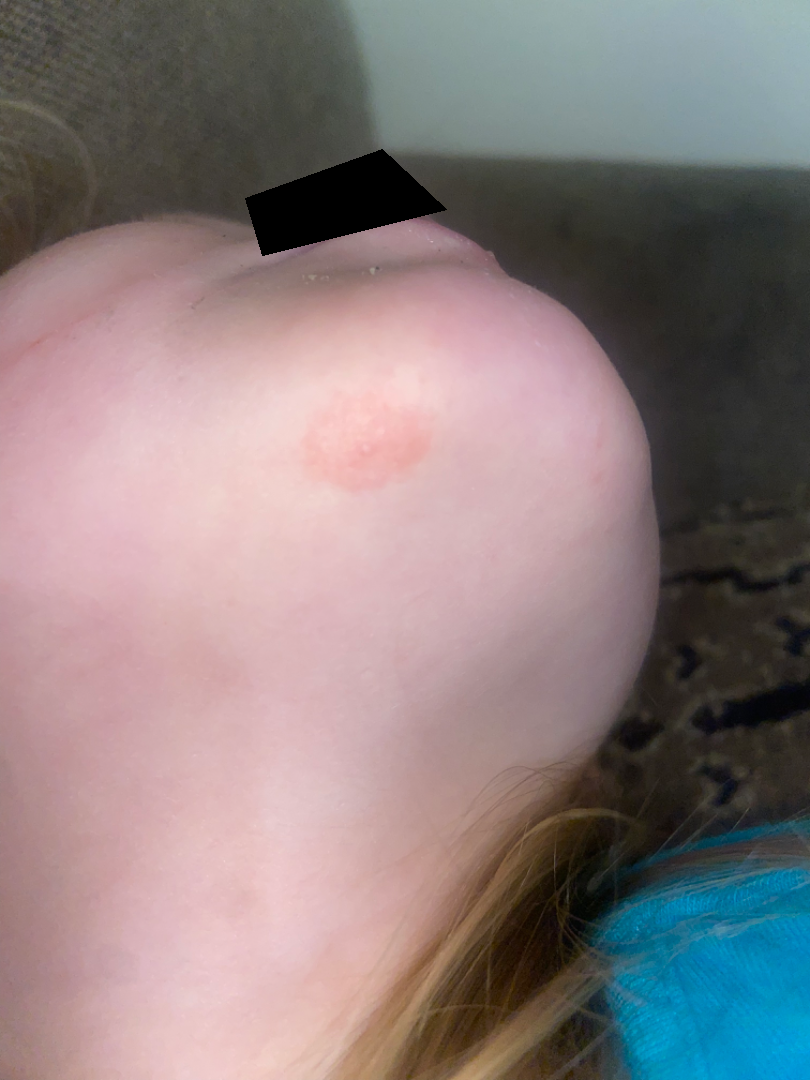Q: Duration?
A: less than one week
Q: Where on the body?
A: head or neck
Q: Texture?
A: rough or flaky
Q: How was the photo taken?
A: close-up
Q: What is the dermatologist's impression?
A: the leading consideration is Eczema; also on the differential is Tinea